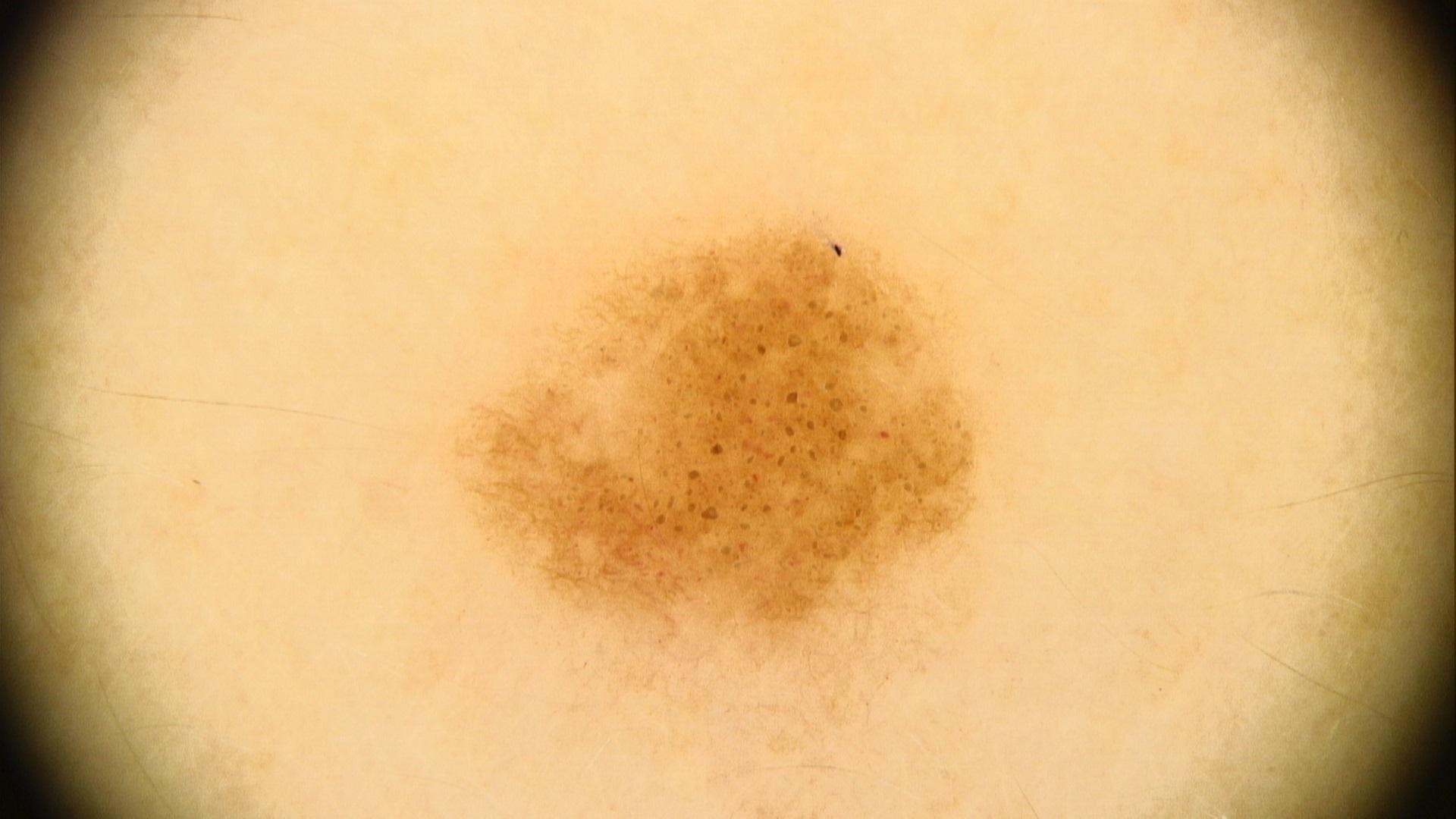A female patient aged 28-32. The patient was assessed as Fitzpatrick skin type III. The lesion was found on the trunk. The clinical assessment was a benign, melanocytic lesion — a nevus.